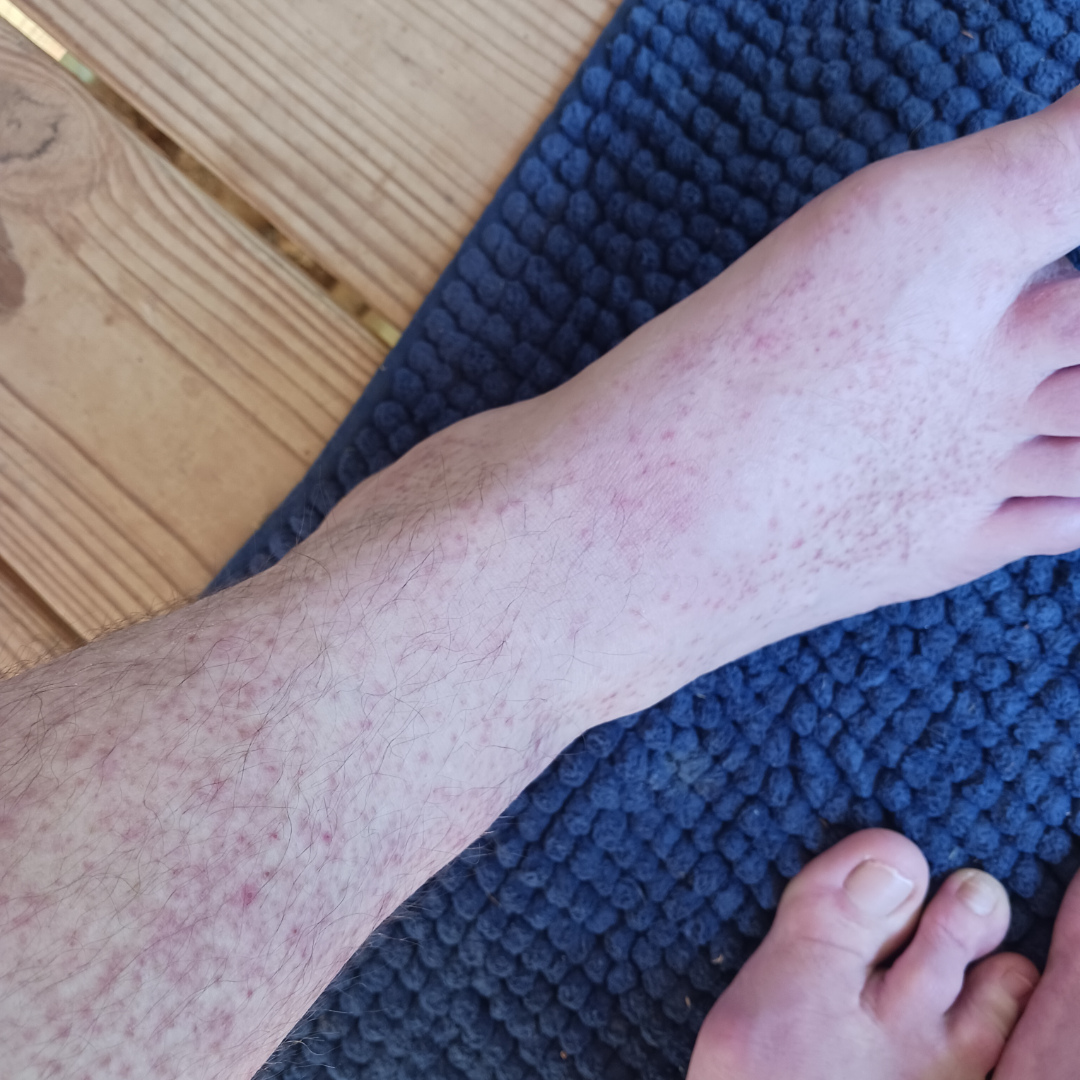• skin tone: Fitzpatrick skin type II; lay graders estimated Monk skin tone scale 2
• associated systemic symptoms: none reported
• anatomic site: top or side of the foot and leg
• framing: close-up
• texture: raised or bumpy
• patient's own categorization: a rash
• diagnostic considerations: the differential, in no particular order, includes Pigmented purpuric eruption, Allergic Contact Dermatitis and Leukocytoclastic Vasculitis